Female subject, age 30–39 · the lesion is described as rough or flaky · reported lesion symptoms include bothersome appearance, bleeding, darkening, pain, enlargement and itching · present for one to three months · self-categorized by the patient as a rash · close-up view · located on the leg:
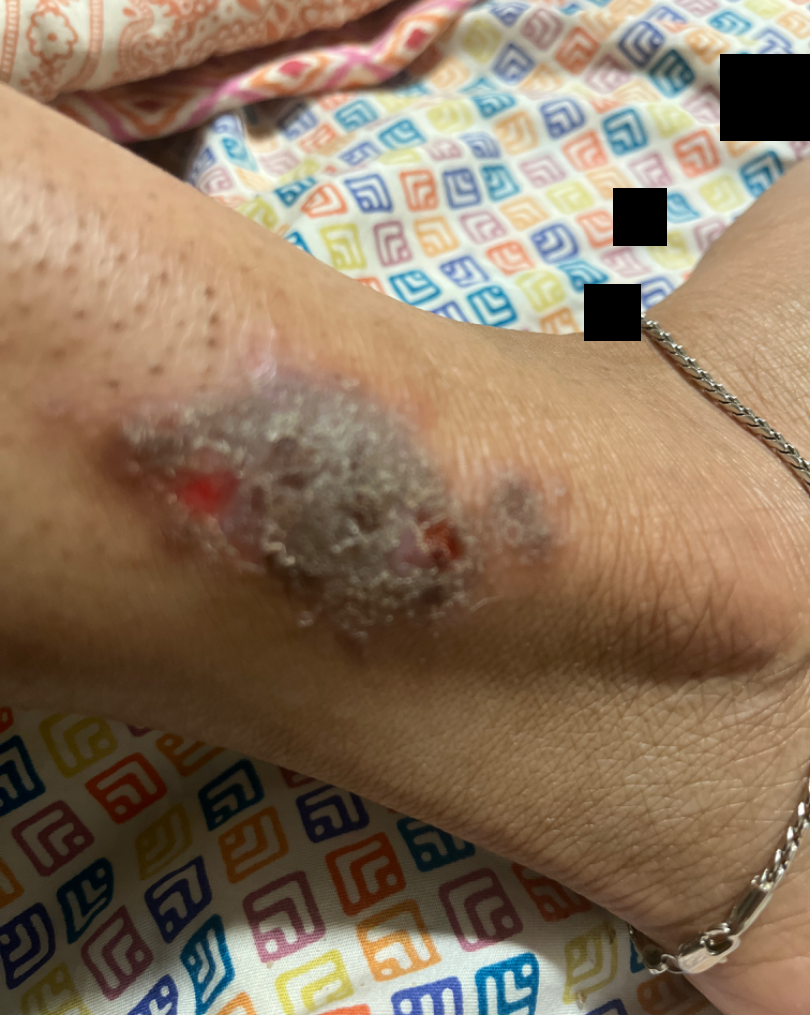differential:
  leading:
    - Lichen Simplex Chronicus
  considered:
    - Mycetoma
  unlikely:
    - Deep fungal infection
    - Lichen planus/lichenoid eruption